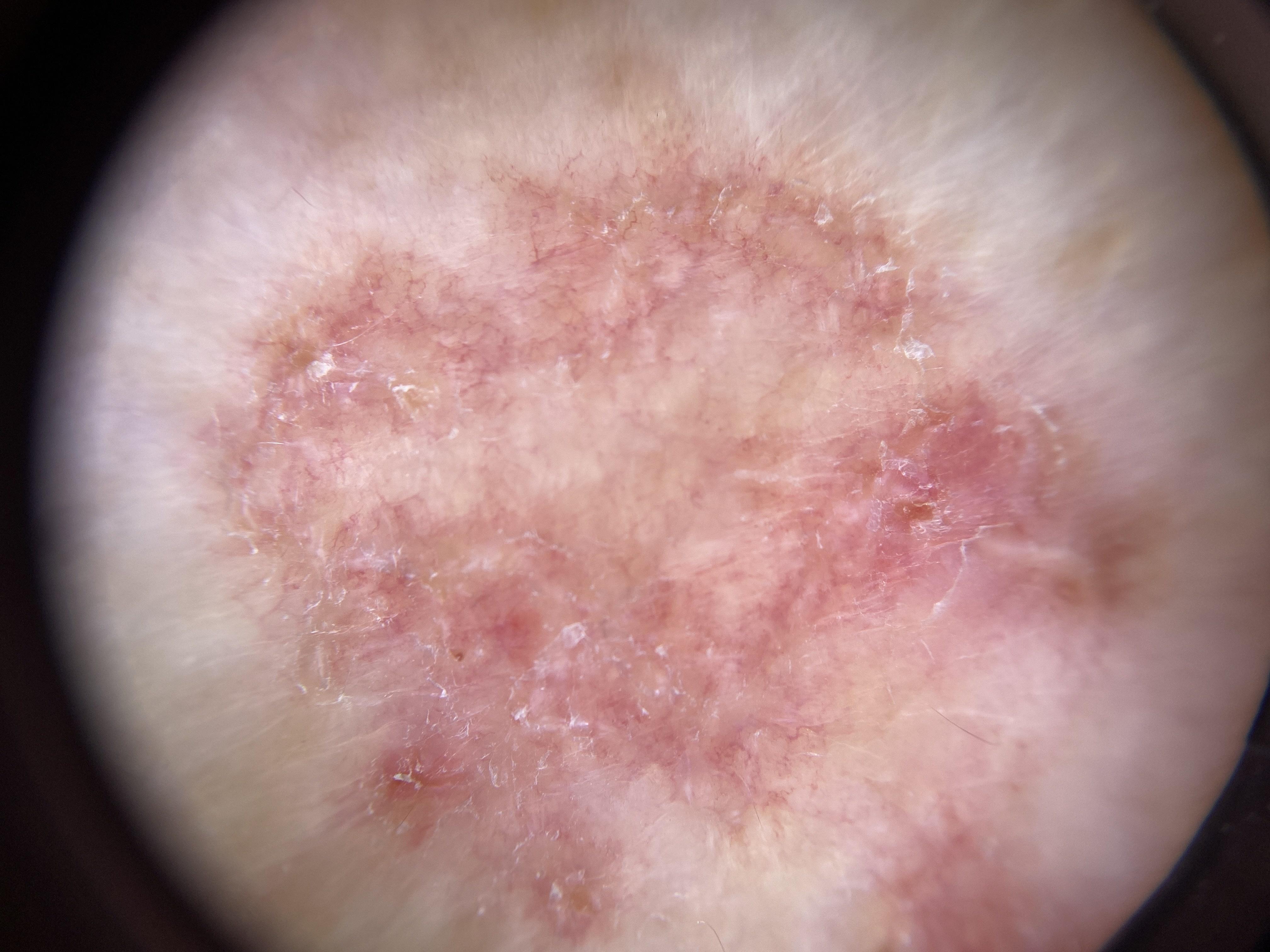Fitzpatrick phototype I. A female patient aged 83 or over. A dermoscopic photograph of a skin lesion. The lesion was found on an upper extremity. Histopathologically confirmed as a malignant, adnexal lesion — a basal cell carcinoma.